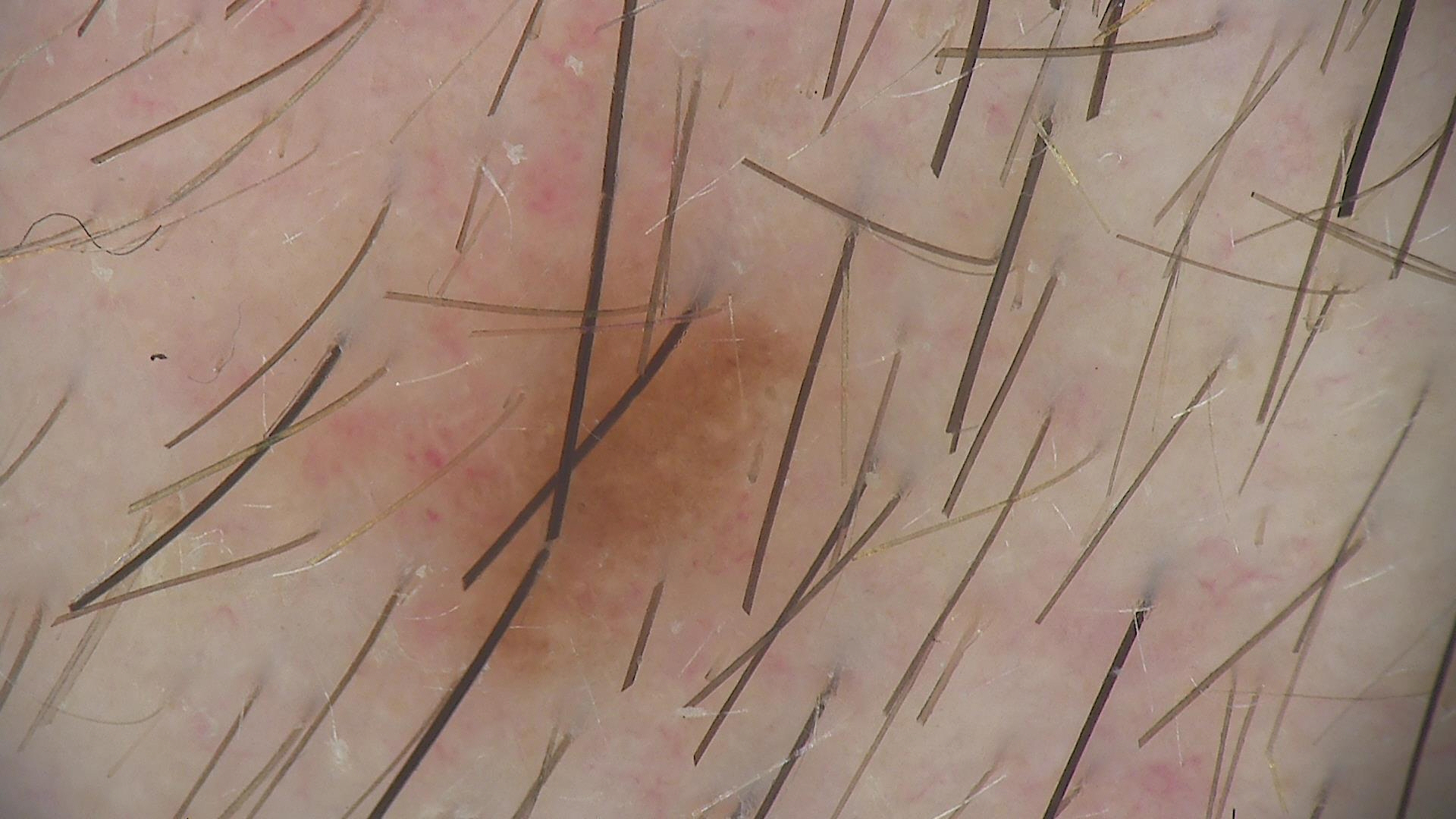Conclusion:
Consistent with a benign lesion — a dysplastic junctional nevus.